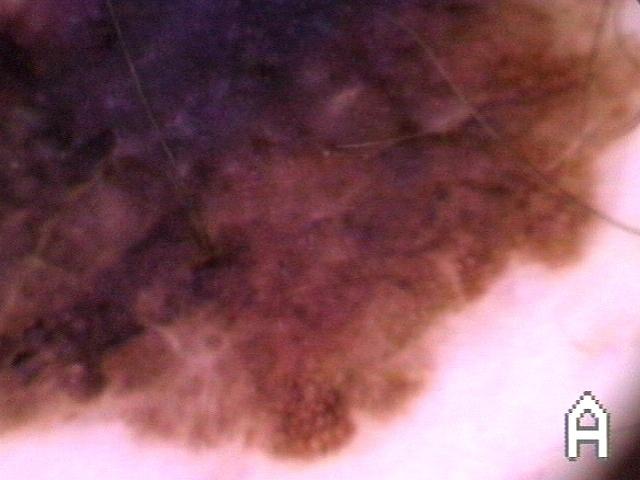modality = contact-polarized dermoscopy
risk factors = a prior melanoma
patient = male, aged 78 to 82
site = the trunk
pathology = Melanoma (biopsy-proven)